By history, prior malignancy (patient or family) · a clinical close-up photograph of a skin lesion · recorded as Fitzpatrick skin type I · a female patient in their 60s:
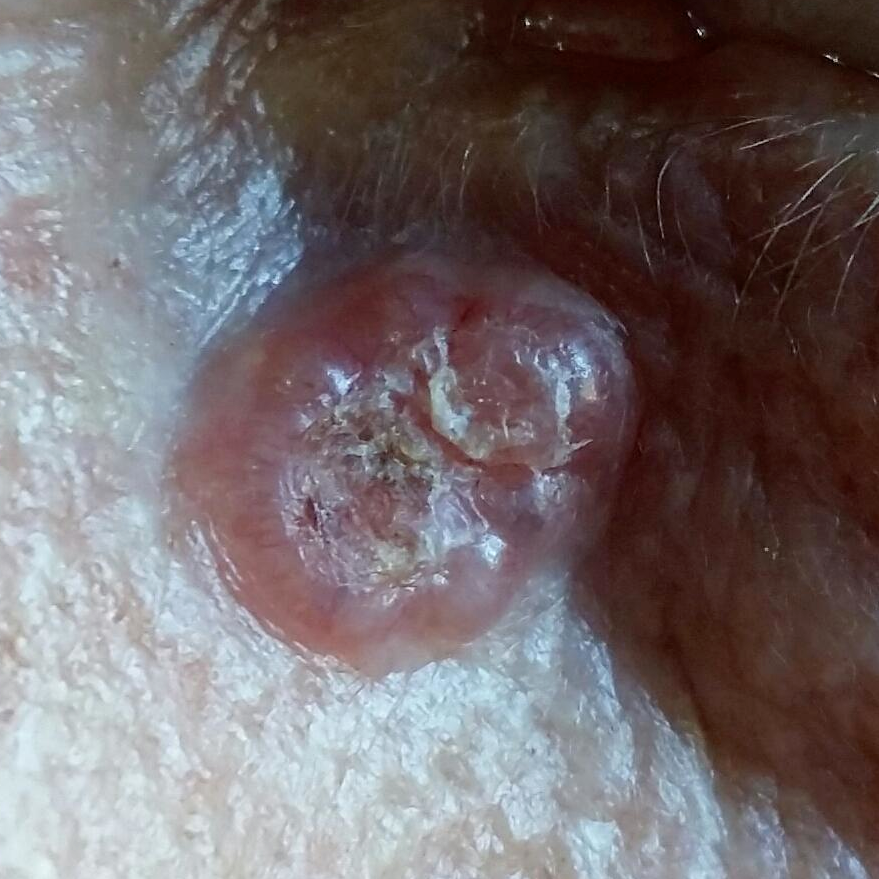Q: What is the anatomic site?
A: the face
Q: What are the lesion's dimensions?
A: 11x7 mm
Q: What symptoms does the patient report?
A: growth, bleeding, elevation, itching
Q: What is the diagnosis?
A: basal cell carcinoma (biopsy-proven)